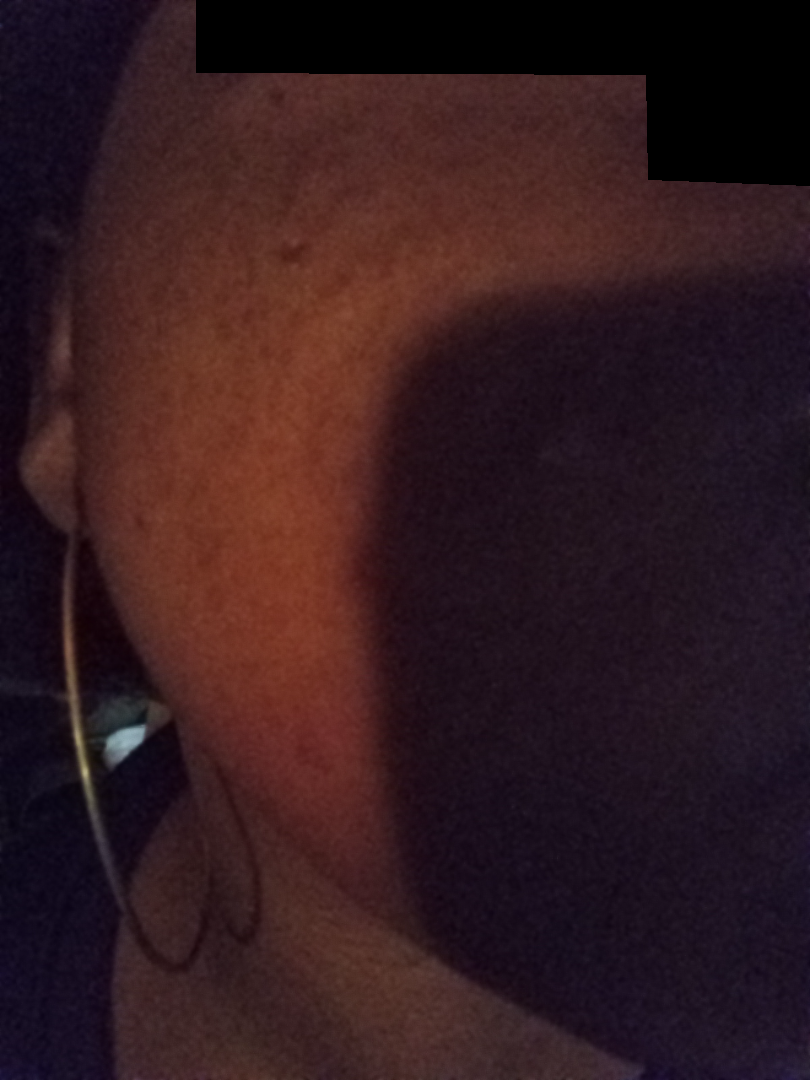The reviewer was unable to grade this case for skin condition.